The contributor is a male aged 40–49, close-up view, located on the leg — 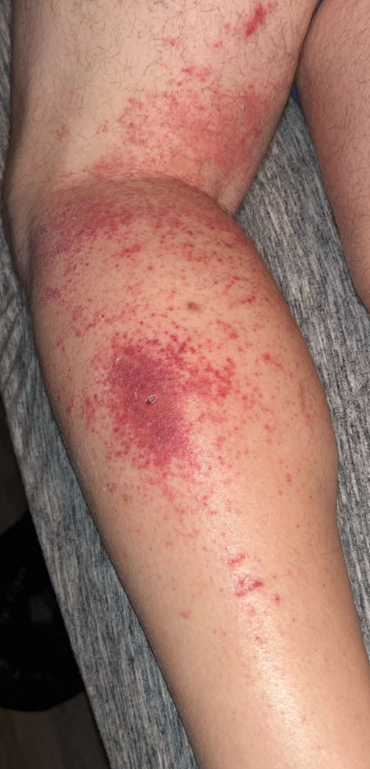Findings: In keeping with Leukocytoclastic Vasculitis.